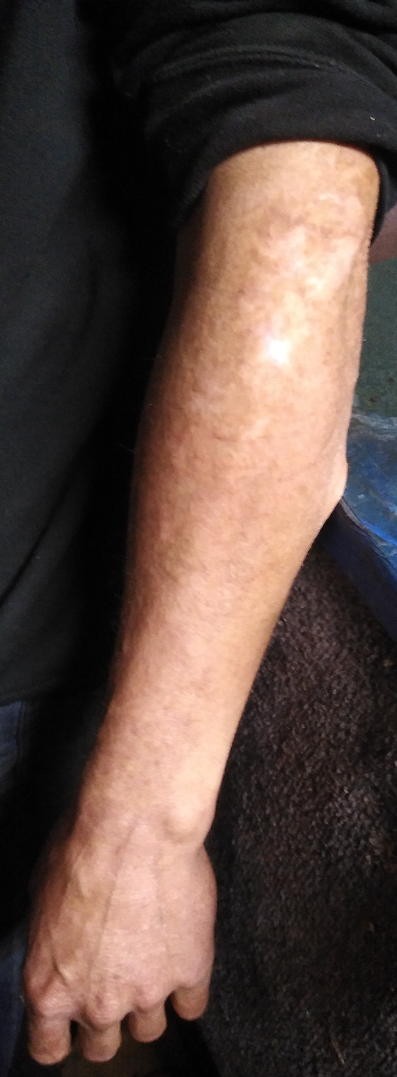The photo was captured at a distance.